A dermoscopy image of a single skin lesion.
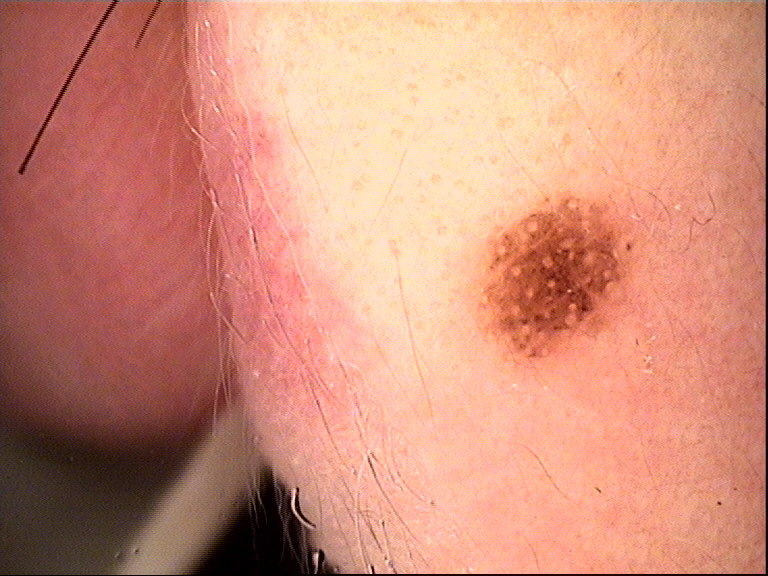subtype = banal, compound | assessment = Miescher nevus (expert consensus).